FST II; a clinical photograph showing a skin lesion; by history, alcohol use; a male subject in their early 70s:
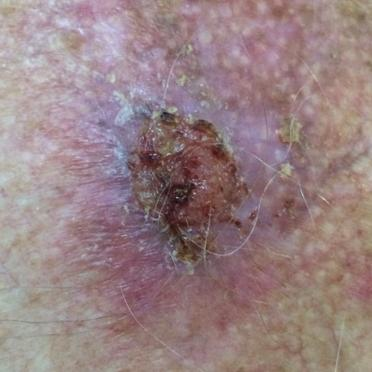Q: What is the anatomic site?
A: the chest
Q: Lesion size?
A: 18 × 13 mm
Q: What did the workup show?
A: squamous cell carcinoma (biopsy-proven)